The subject is a female aged 30–39, located on the front of the torso, close-up view: 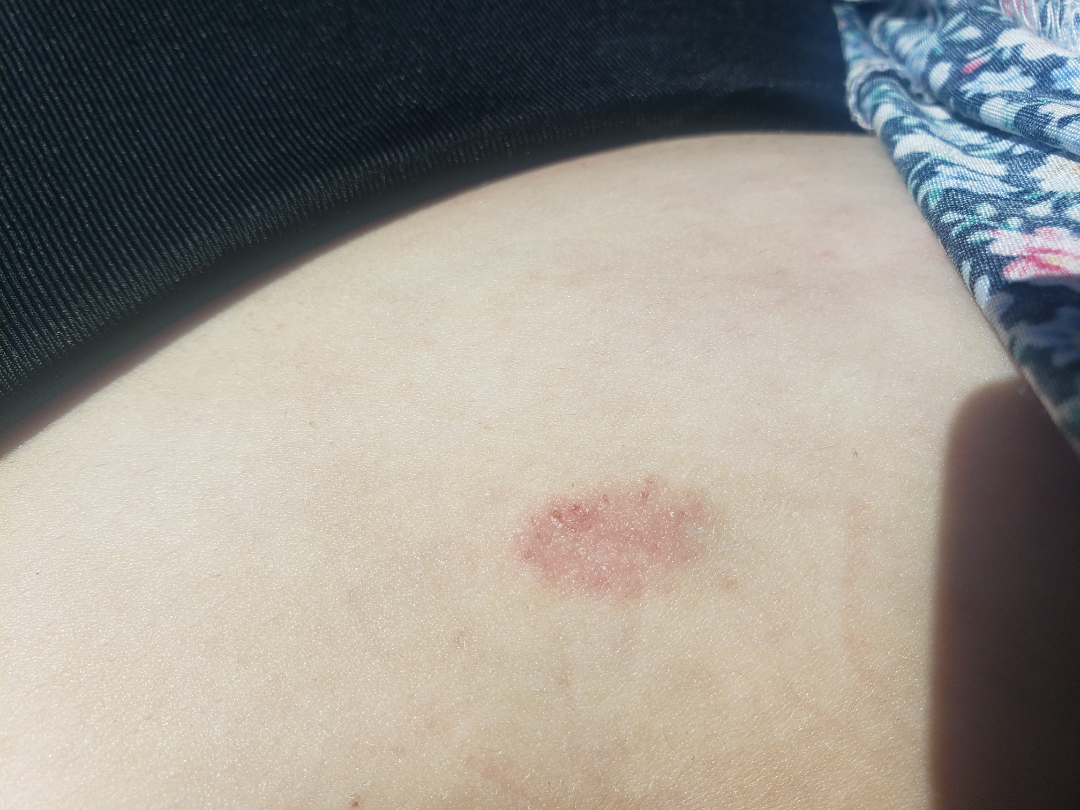The contributor notes the condition has been present for less than one week. Skin tone: Fitzpatrick II; lay graders estimated 2 on the Monk Skin Tone. The patient considered this a rash. Symptoms reported: itching and darkening. On remote review of the image, Eczema (primary).